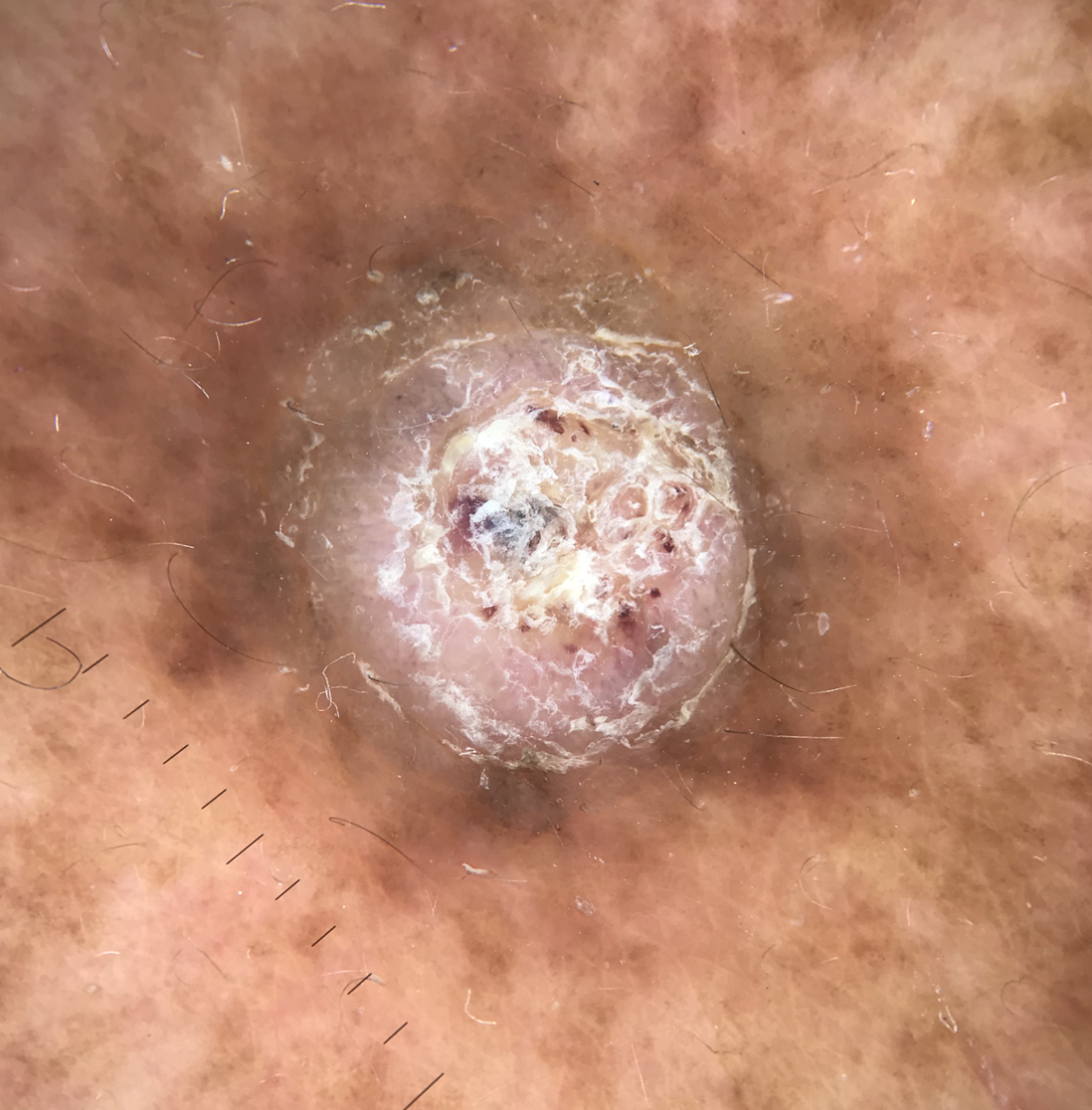Q: What kind of image is this?
A: dermoscopy
Q: What is the lesion category?
A: keratinocytic
Q: What did the workup show?
A: cutaneous horn (biopsy-proven)